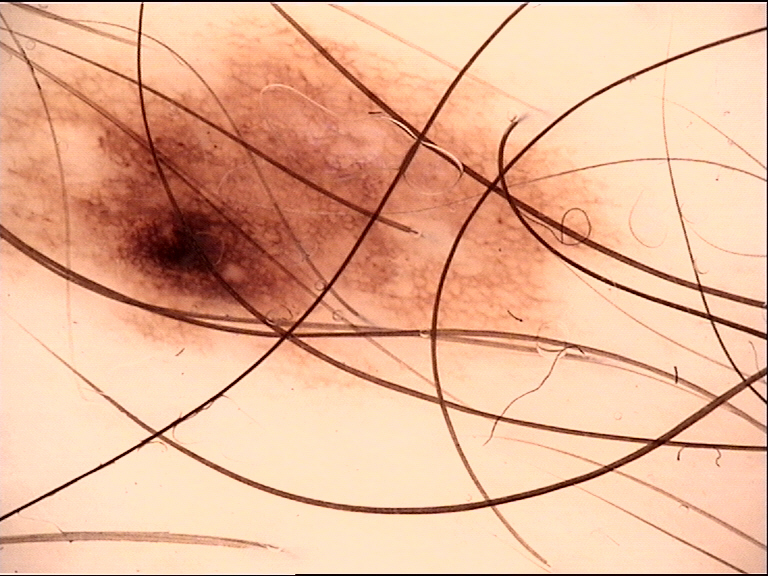The diagnostic label was a benign lesion — a dysplastic junctional nevus.